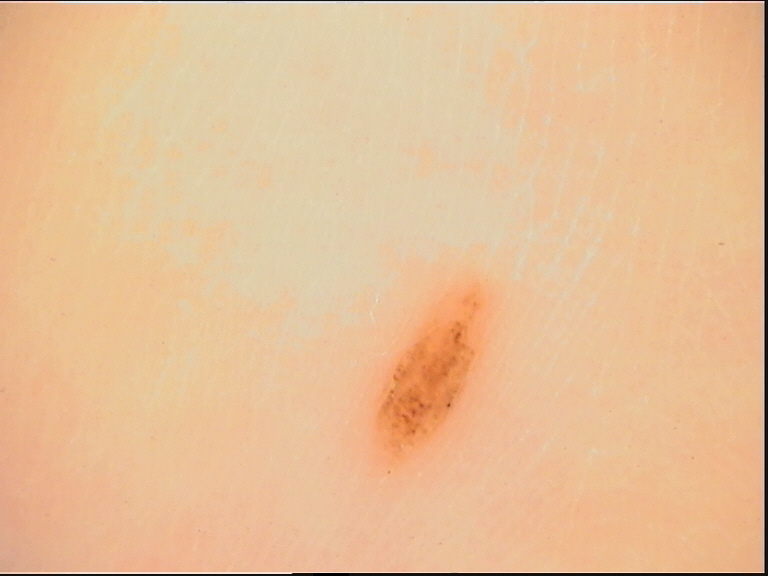– image — dermoscopy
– class — acral dysplastic junctional nevus (expert consensus)